A skin lesion imaged with a dermatoscope. The patient describes having a moderate number of moles. Imaged for a research study, with no referral diagnosis recorded. The patient says their skin tans without first burning. A male subject 72 years of age — 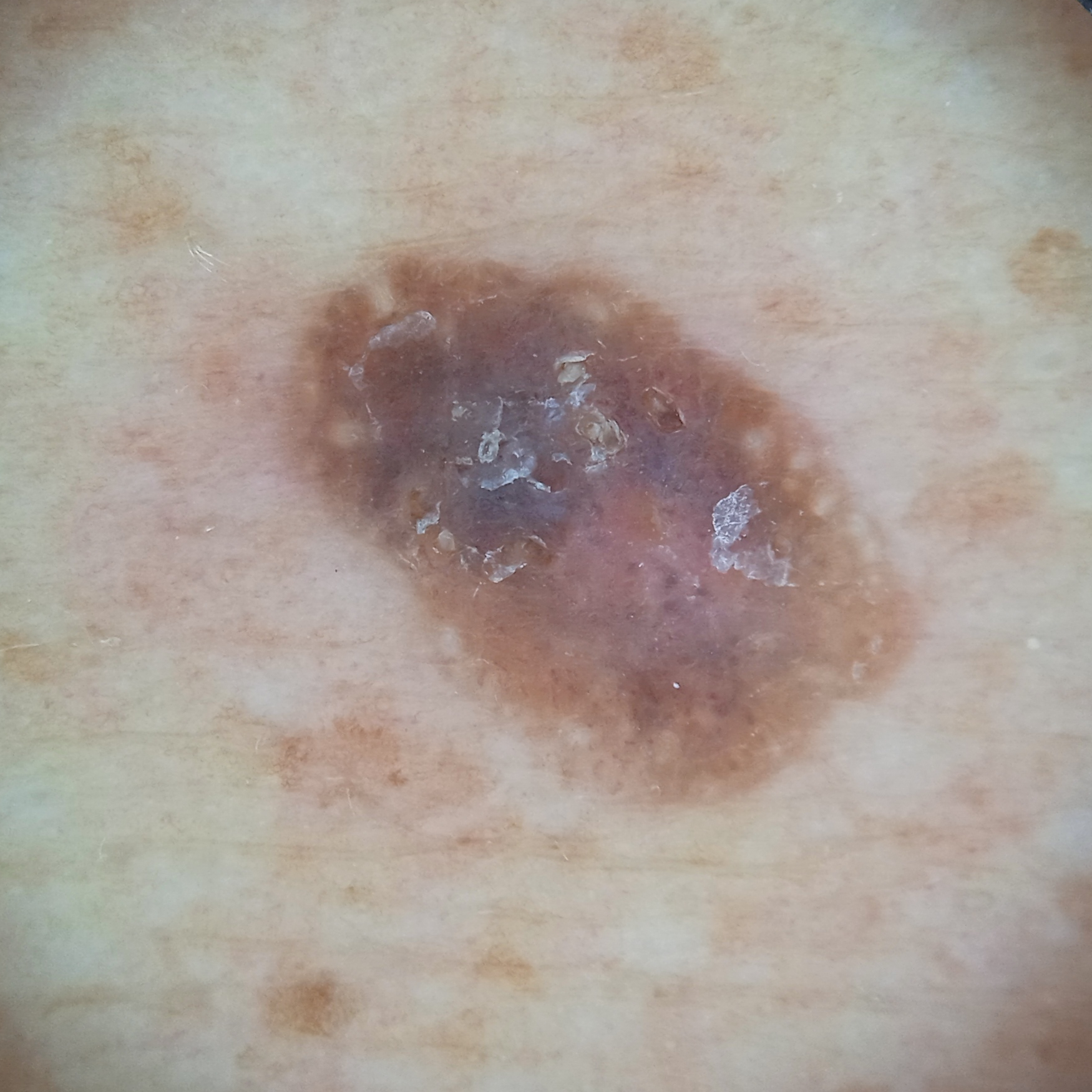Located on the back.
Measuring roughly 8.1 mm.
The lesion was assessed as a seborrheic keratosis.